This image was taken at a distance.
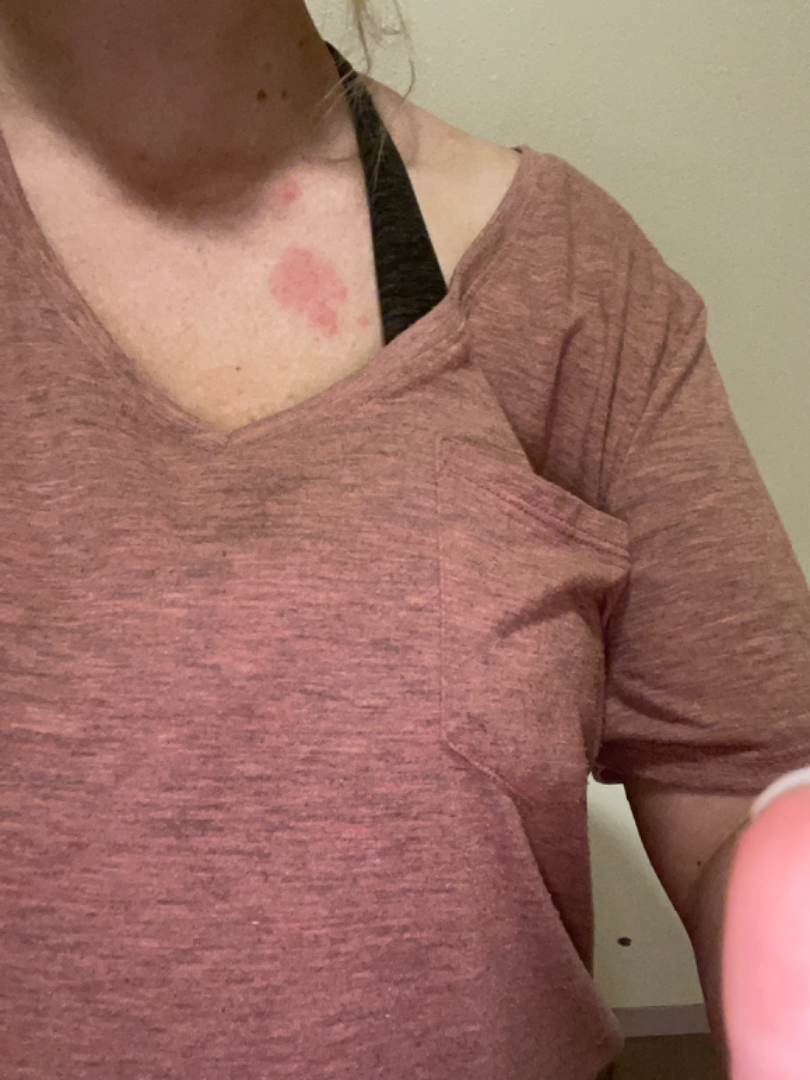Findings:
The leading consideration is Insect Bite; also consider Urticaria; lower on the differential is Allergic Contact Dermatitis.